This is a close-up image — 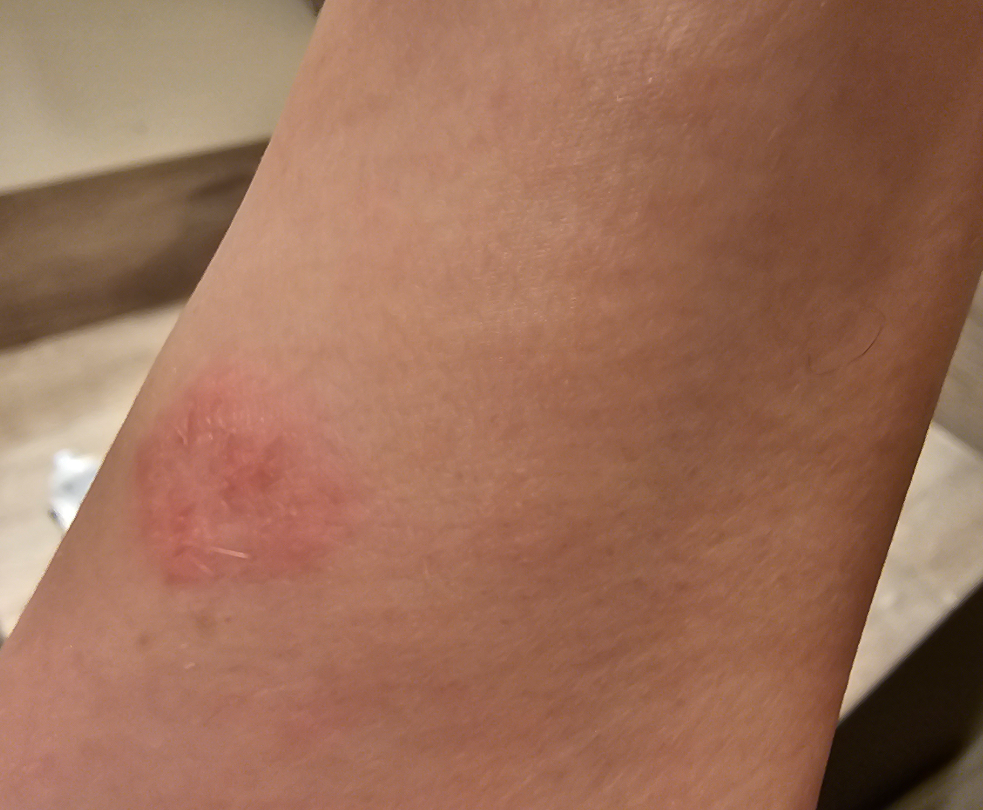Reviewed remotely by one dermatologist: most likely Basal Cell Carcinoma; possibly SCC/SCCIS; a remote consideration is Infected eczema.